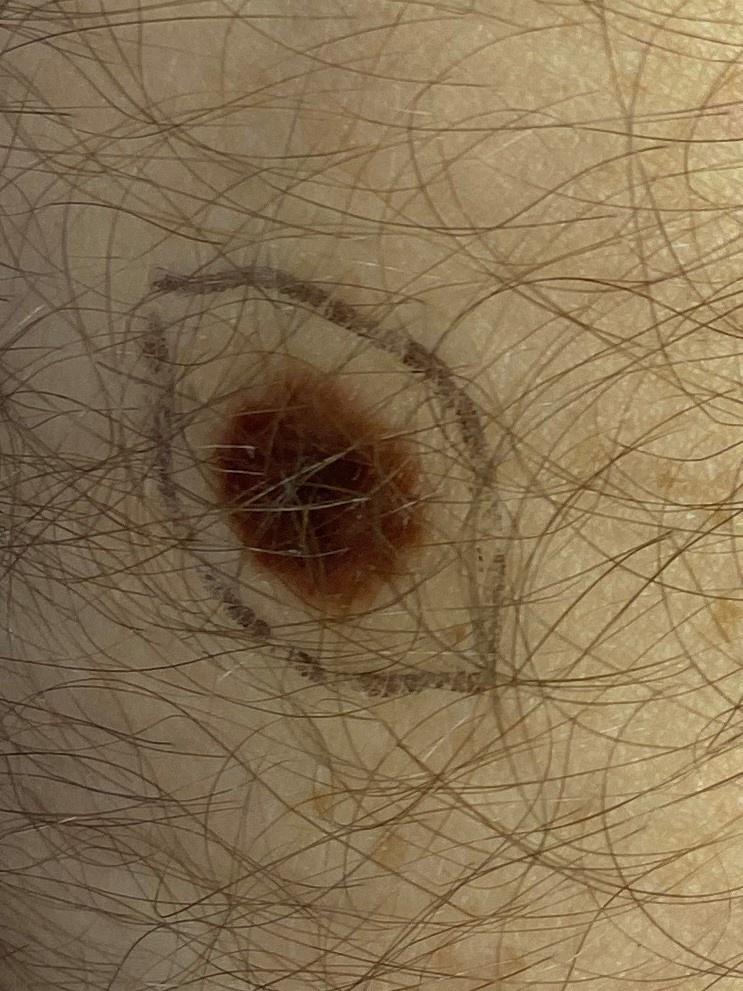Q: What is this lesion?
A: Nevus (biopsy-proven)